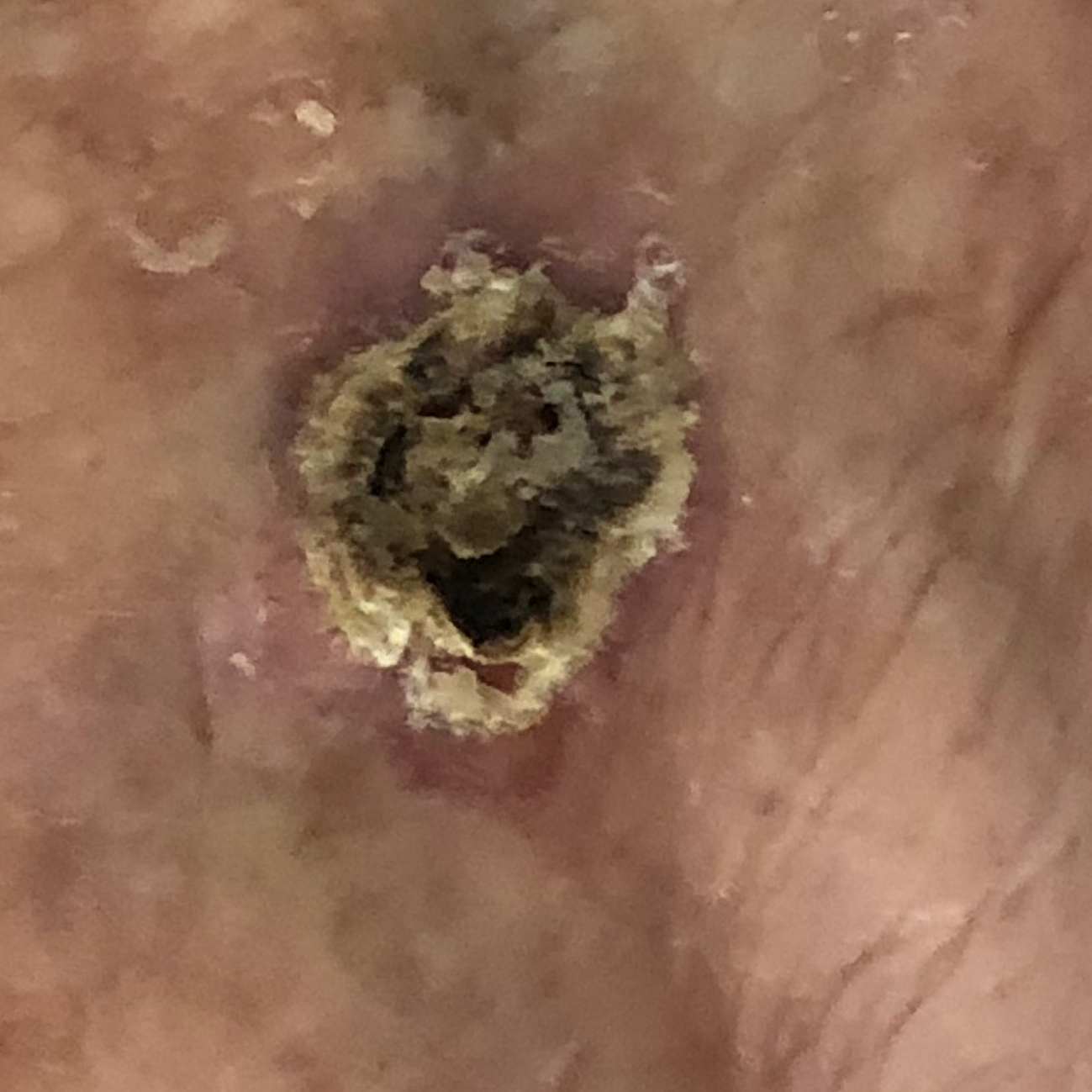Recorded as FST II. A female subject in their 70s. A clinical photograph of a skin lesion. The lesion is located on a hand. Measuring about 15 × 13 mm. Per patient report, the lesion is elevated, but has not changed. Histopathology confirmed a lesion of indeterminate malignant potential — an actinic keratosis.